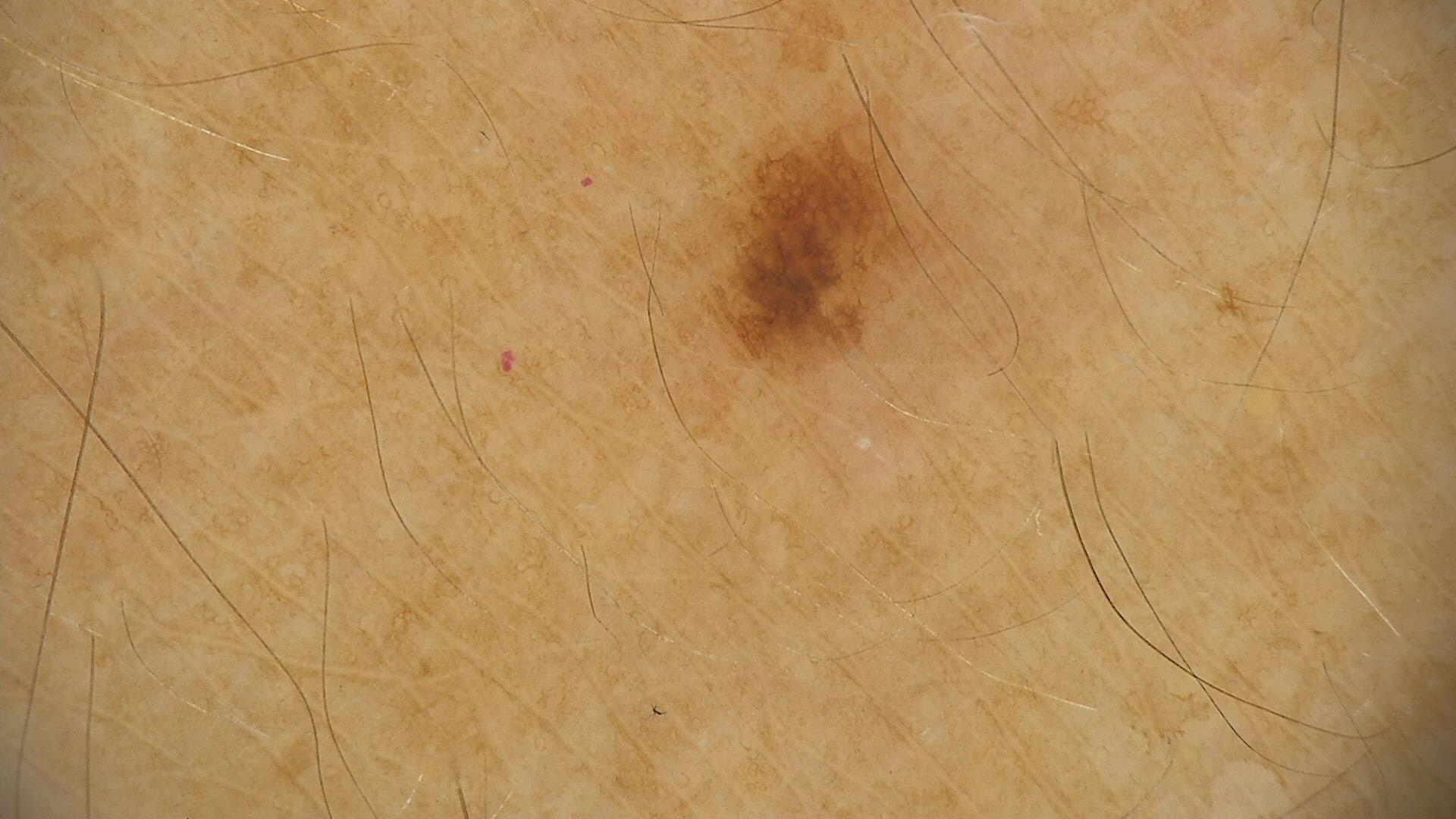Findings:
A dermoscopy image of a single skin lesion.
Conclusion:
The diagnostic label was a dysplastic junctional nevus.